The chart notes a previous melanoma. A male patient aged approximately 60. A contact-polarized dermoscopy image of a skin lesion — 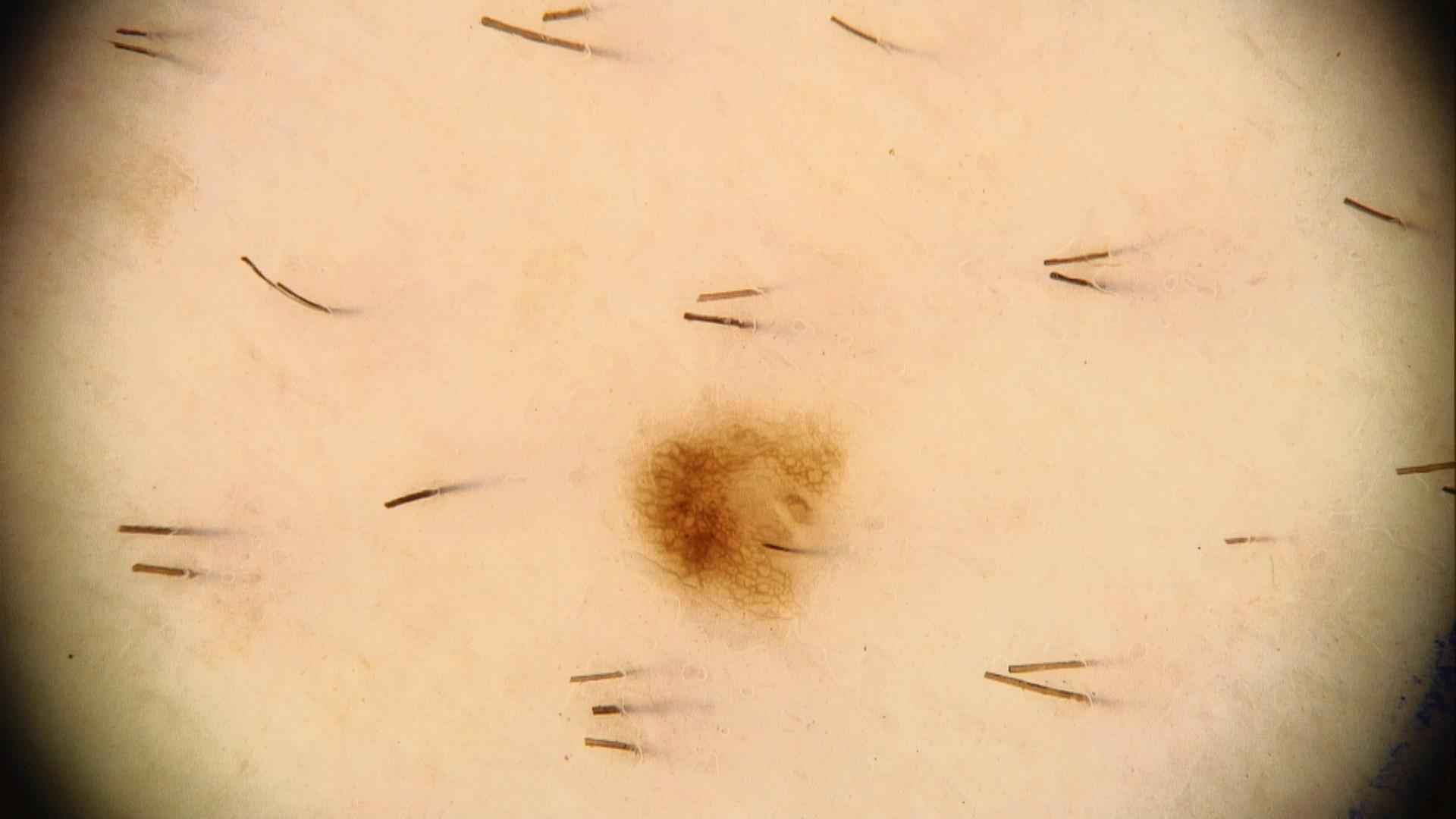The lesion is on the trunk.
The clinical assessment was a benign lesion — a nevus.